A dermoscopy image of a single skin lesion.
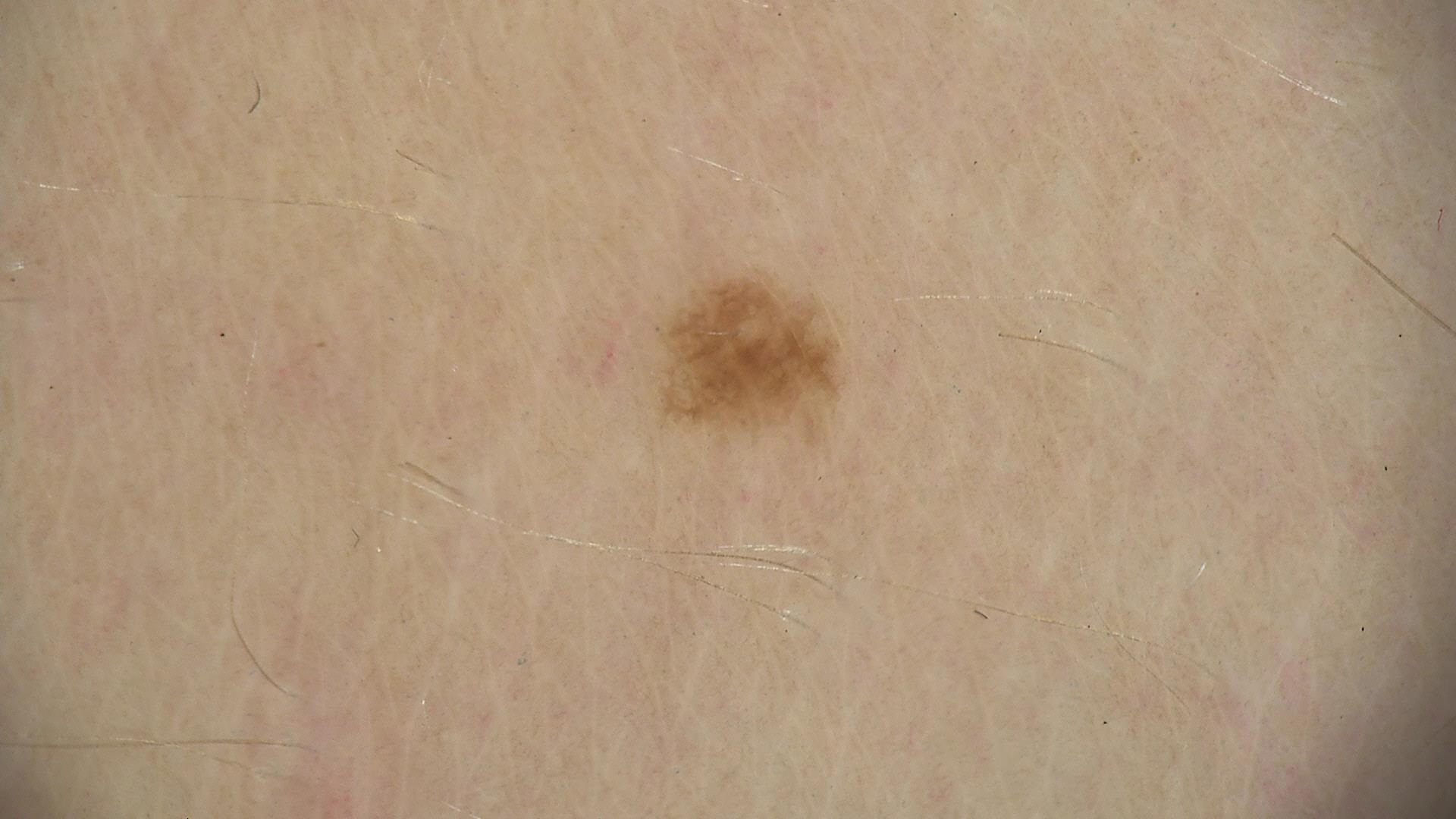Case:
The morphology is that of a banal lesion.
Conclusion:
Diagnosed as a junctional nevus.